Close-up view; the affected area is the leg:
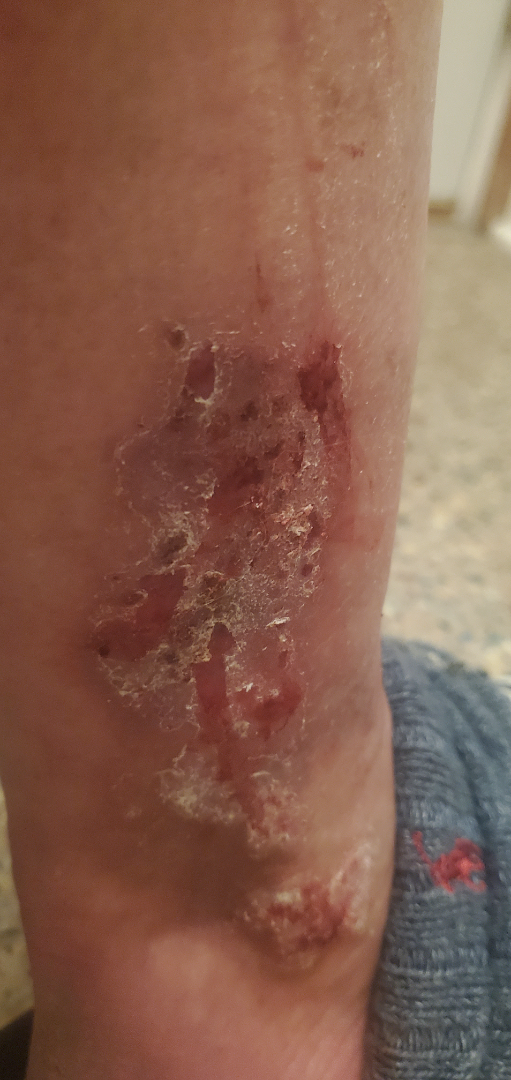The case was difficult to assess from the available photograph. The condition has been present for more than one year. The patient indicates burning, bothersome appearance, itching, enlargement, darkening and pain. The patient indicates associated joint pain. The patient considered this a rash.